The photo was captured at an angle; the patient considered this a rash; skin tone: Fitzpatrick skin type III; texture is reported as raised or bumpy; the affected area is the arm.
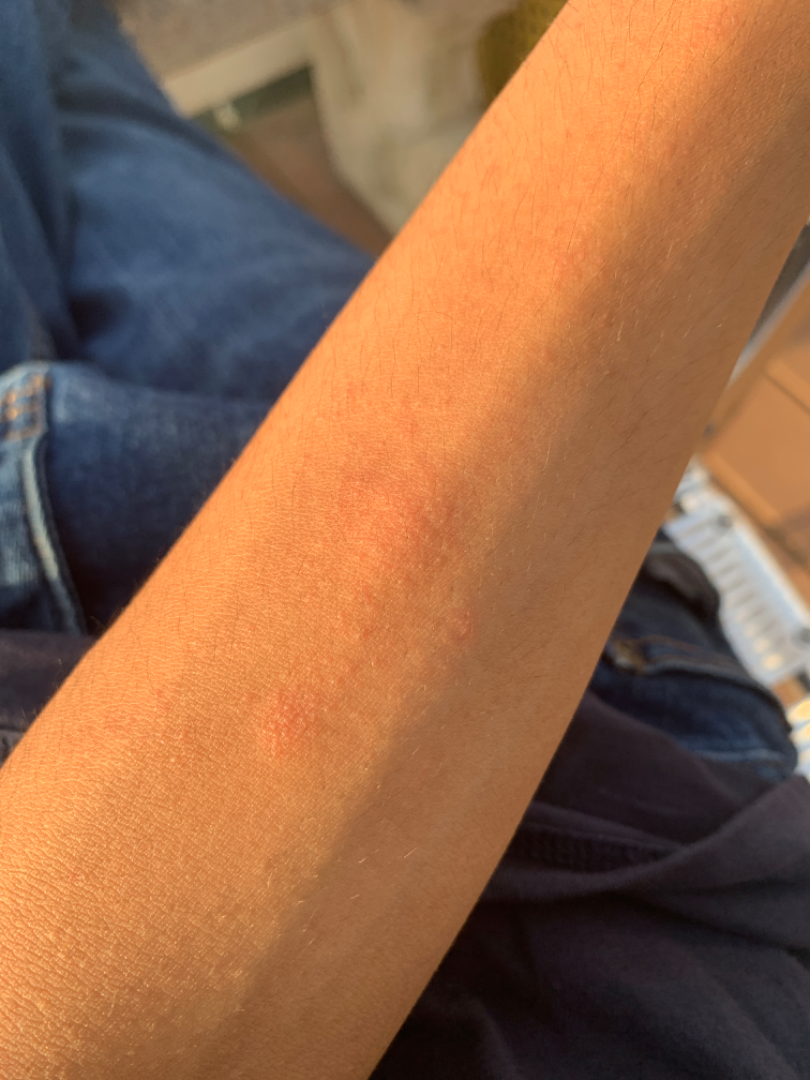Assessment: The image was not sufficient for the reviewer to characterize the skin condition.